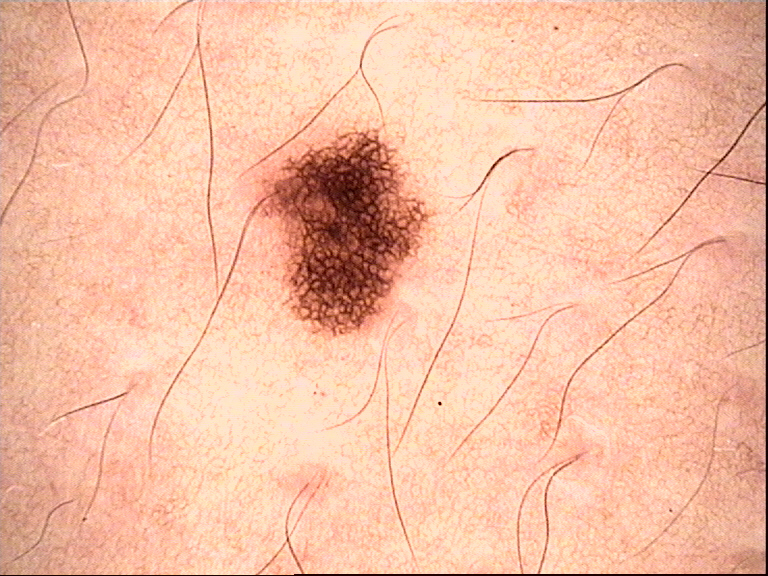modality: dermatoscopy
class: dysplastic junctional nevus (expert consensus)